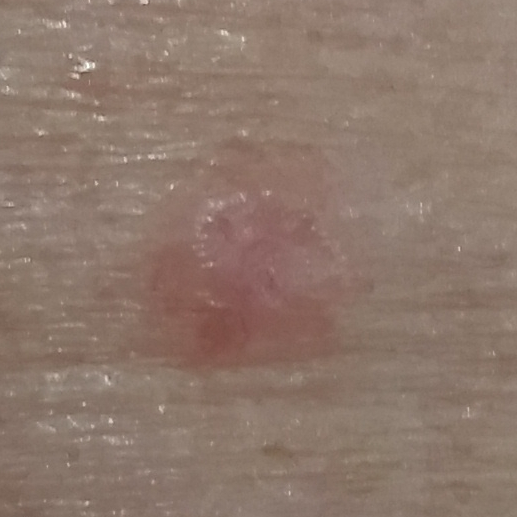A clinical close-up photograph of a skin lesion.
A female patient age 70.
By history, prior malignancy (patient or family) and no pesticide exposure.
The lesion was found on the face.
The lesion measures 5 × 5 mm.
The patient reports that the lesion is elevated.
Histopathological examination showed a malignant skin lesion — a basal cell carcinoma.